Collected as part of a research study, without a referral diagnosis · a female patient 84 years of age — 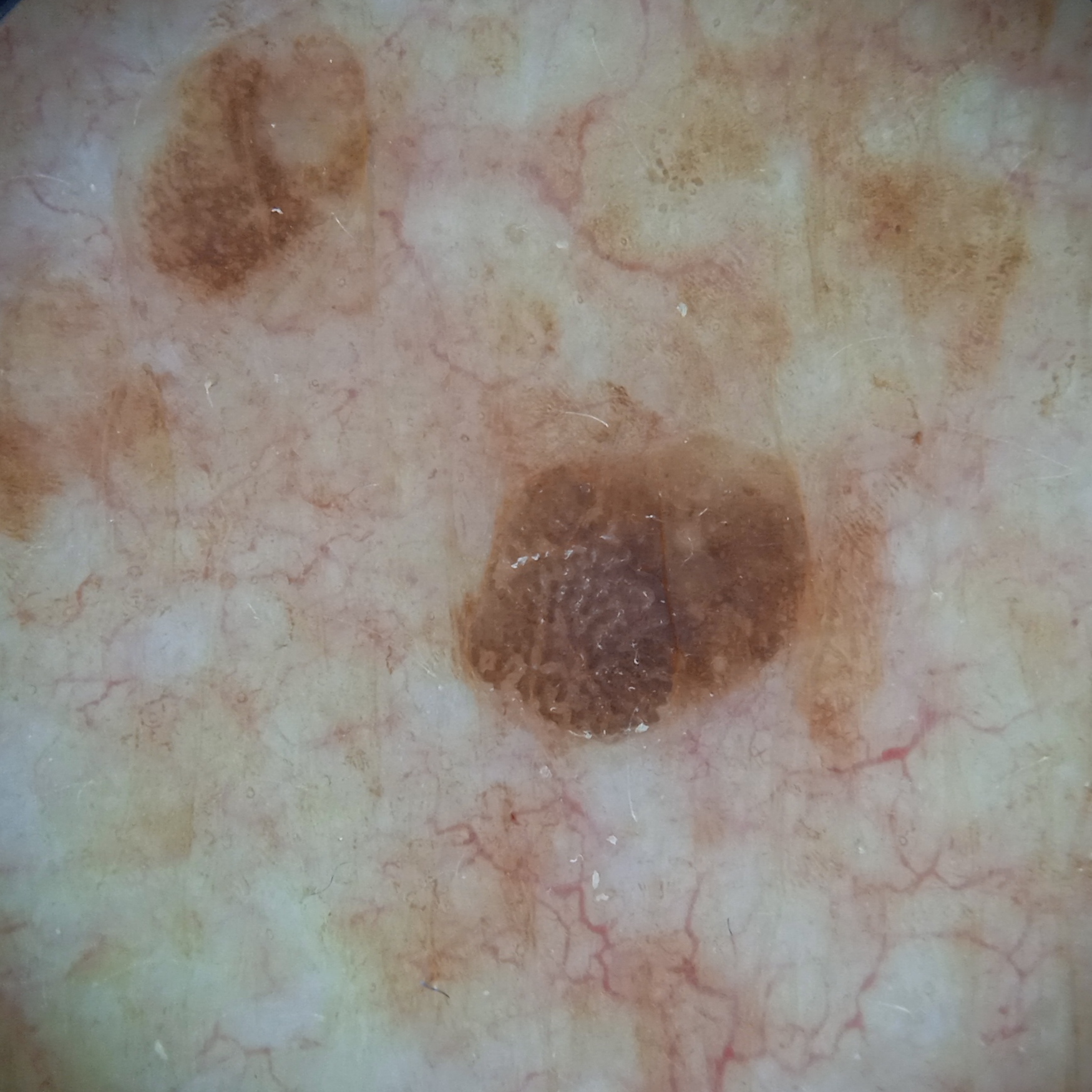The lesion involves the torso. The lesion was assessed as a seborrheic keratosis.